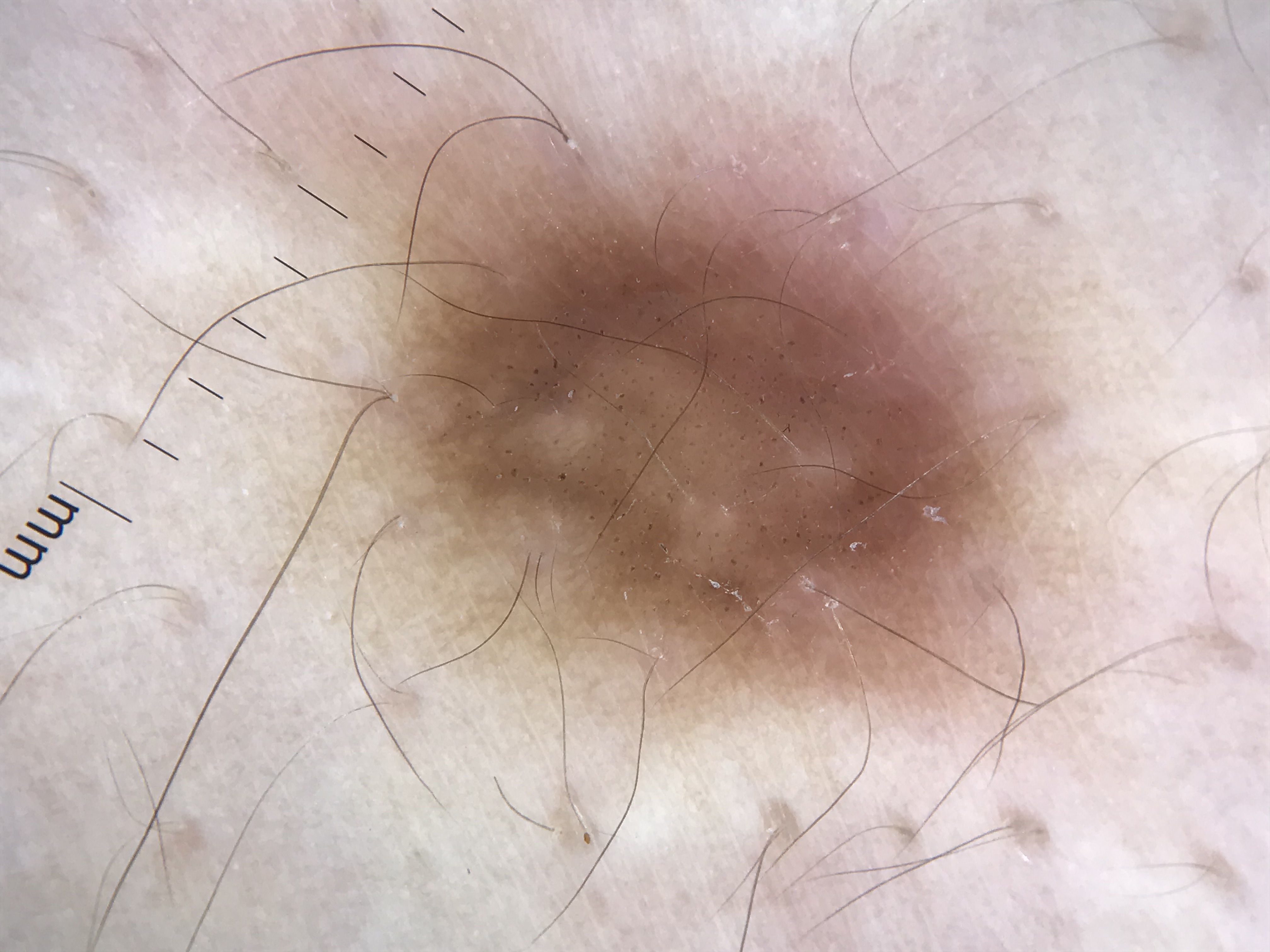Diagnosed as a fibro-histiocytic lesion — a dermatofibroma.